This image was taken at an angle; the subject is 30–39, female; the affected area is the arm.
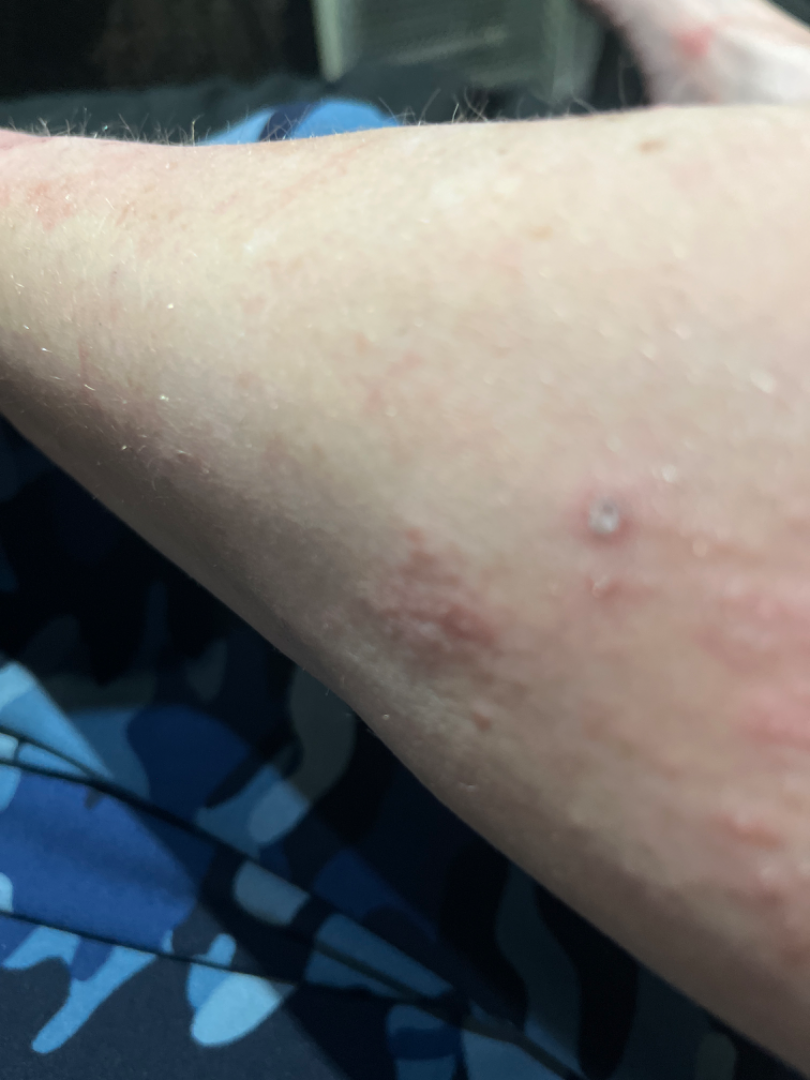The differential includes Psoriasis, Eczema and Lichen Simplex Chronicus, with no clear leading consideration.